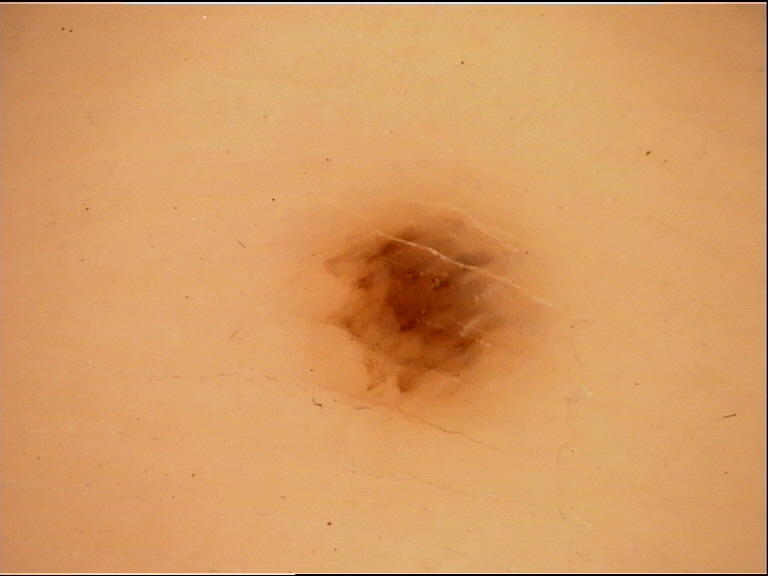Conclusion: Diagnosed as an acral junctional nevus.